The patient is skin type II; a dermoscopic close-up of a skin lesion: 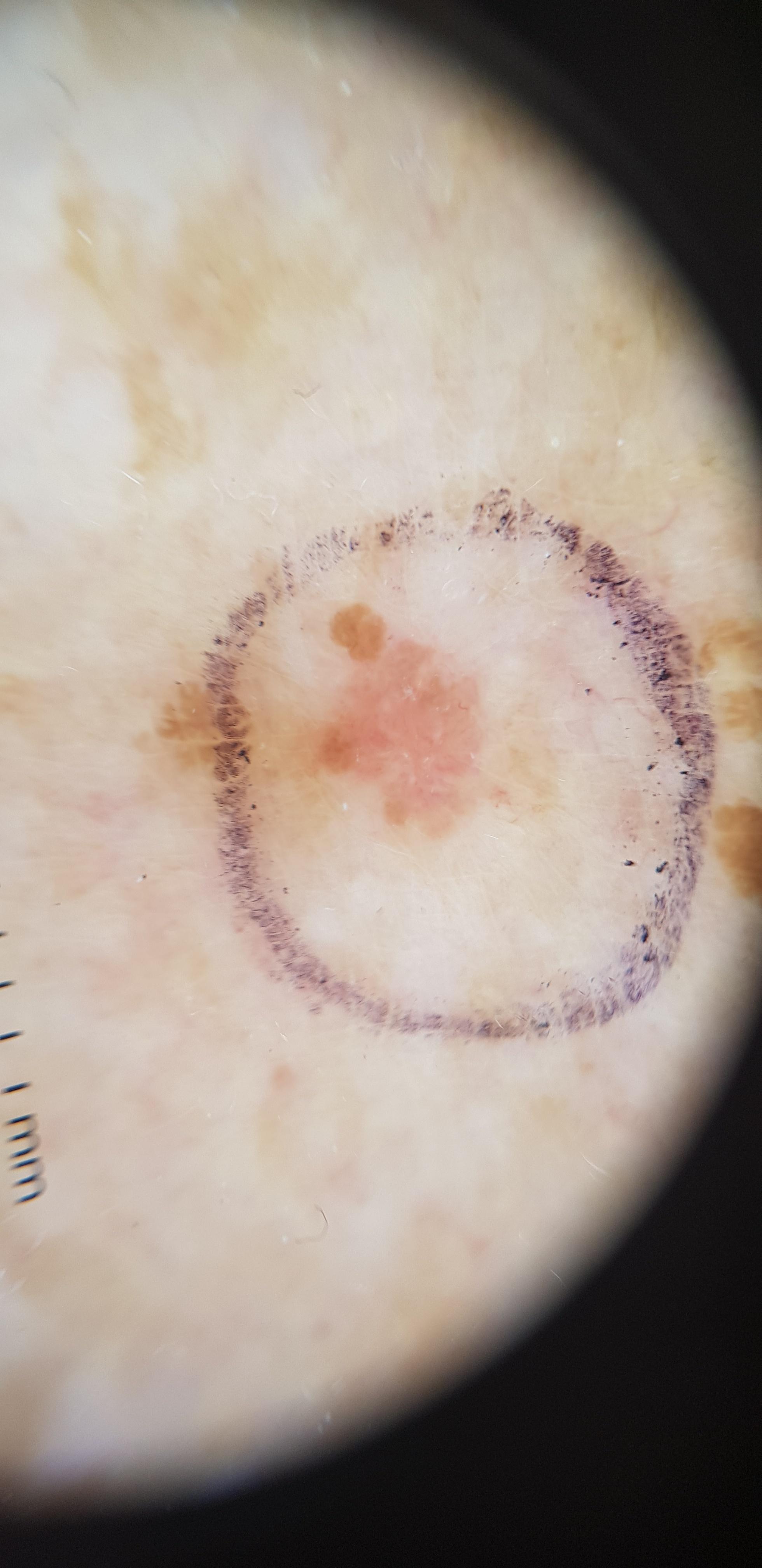Located on the trunk. Histopathology confirmed a malignant lesion — a squamous cell carcinoma.